Close-up view — 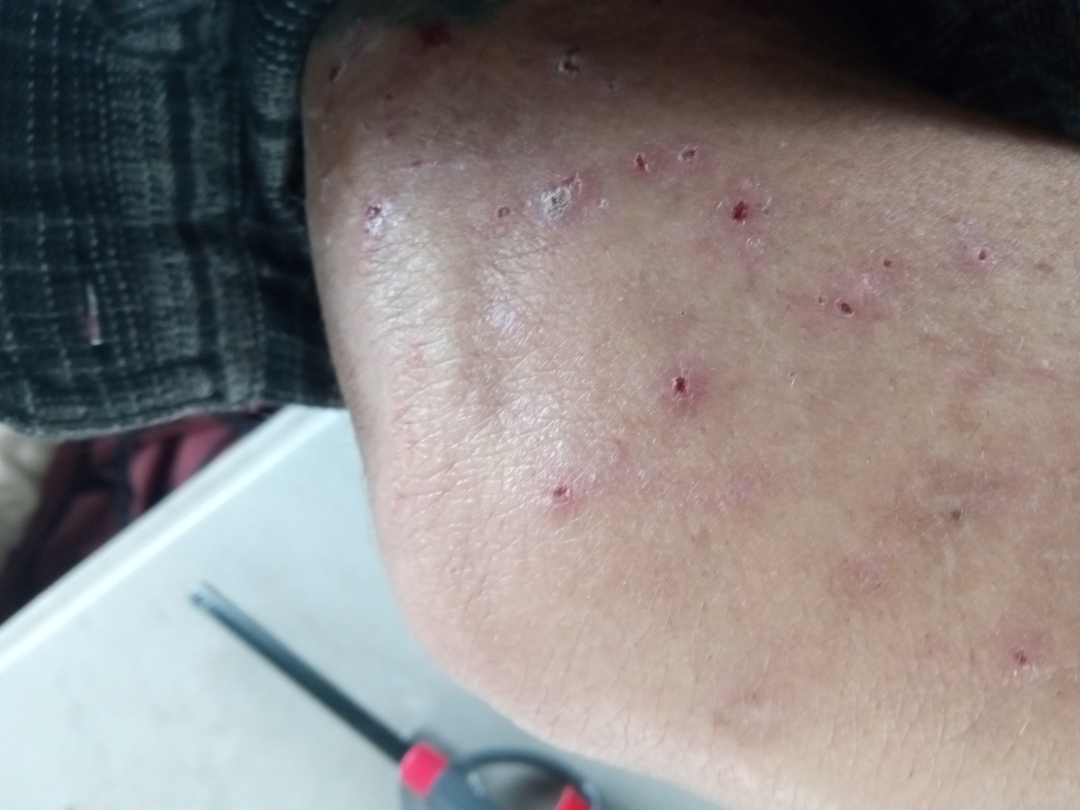Q: What is the differential diagnosis?
A: Dermatitis herpetiformis, Prurigo nodularis and Folliculitis were considered with similar weight